The patient described the issue as a rash · no relevant lesion symptoms reported · this is a close-up image · the leg is involved: 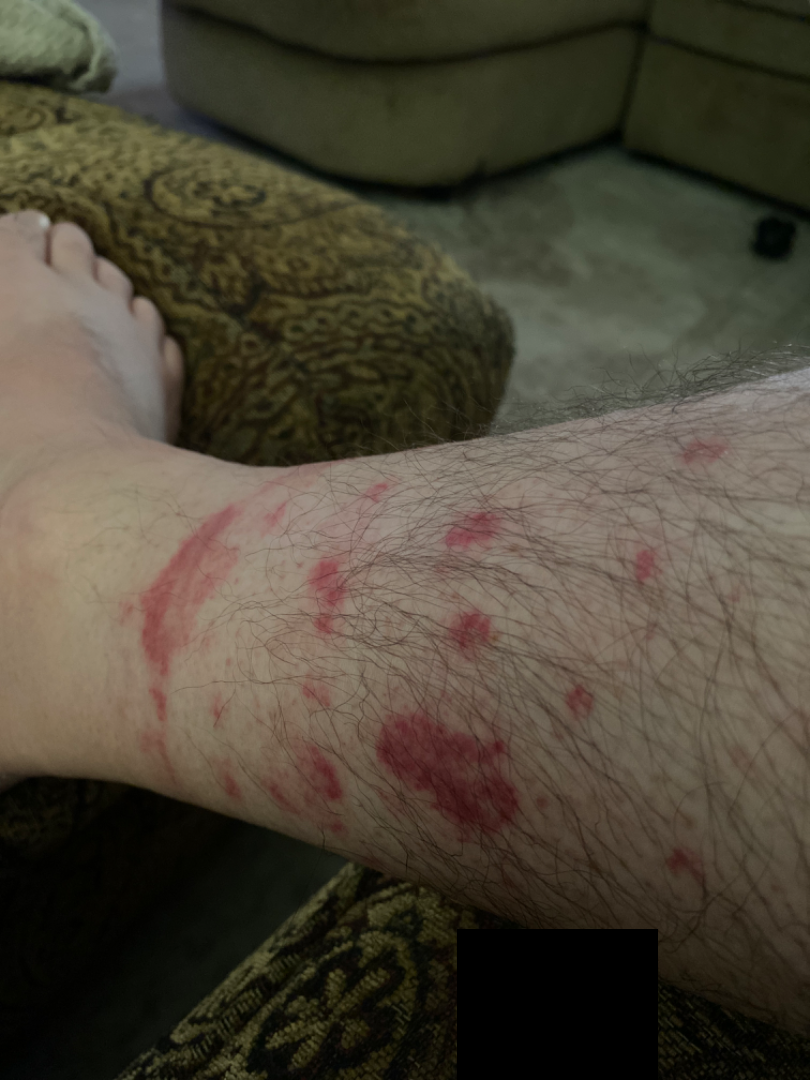Q: What is the differential diagnosis?
A: Pigmented purpuric eruption (primary)